Skin type III · a male patient aged 58-62 · a dermoscopic photograph of a skin lesion.
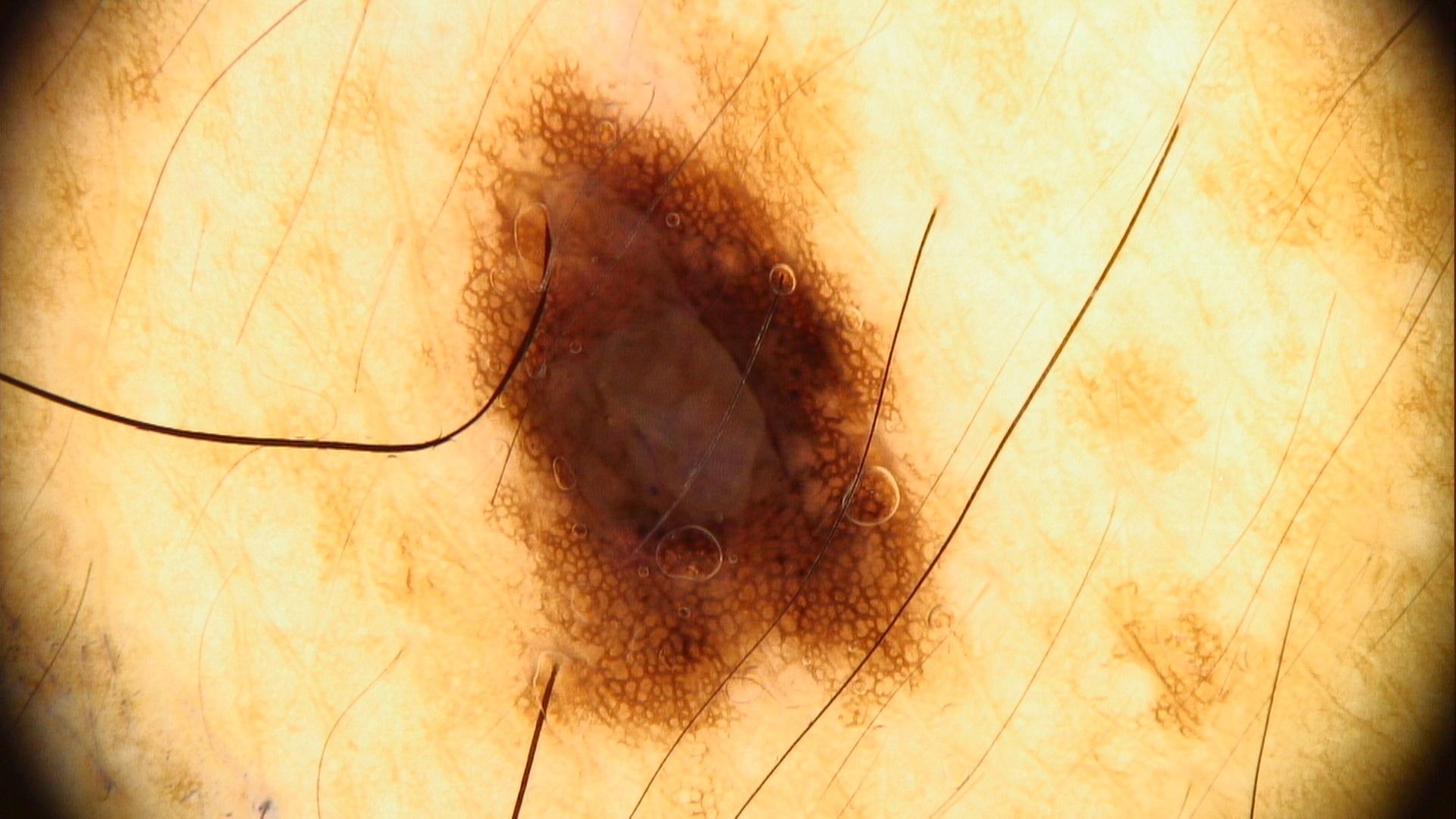The clinical impression was a benign, melanocytic lesion — a nevus.